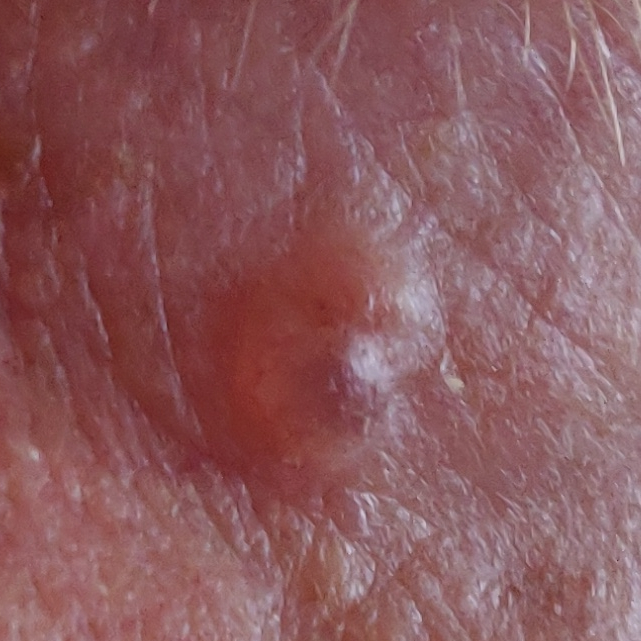FST = I
exposure history = no tobacco use
subject = male, age 76
imaging = clinical photo
site = the face
size = 6x4 mm
symptoms = itching, growth, elevation
pathology = basal cell carcinoma (biopsy-proven)